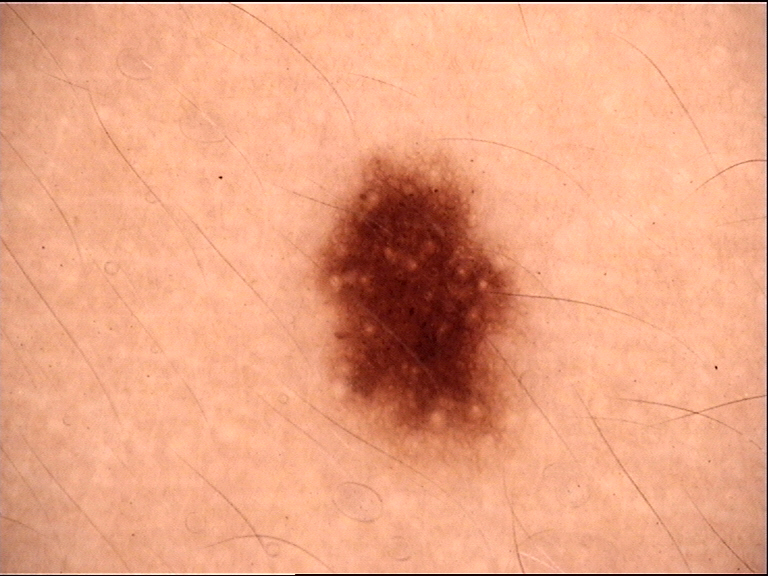A skin lesion imaged with a dermatoscope. The diagnosis was a benign lesion — a dysplastic junctional nevus.